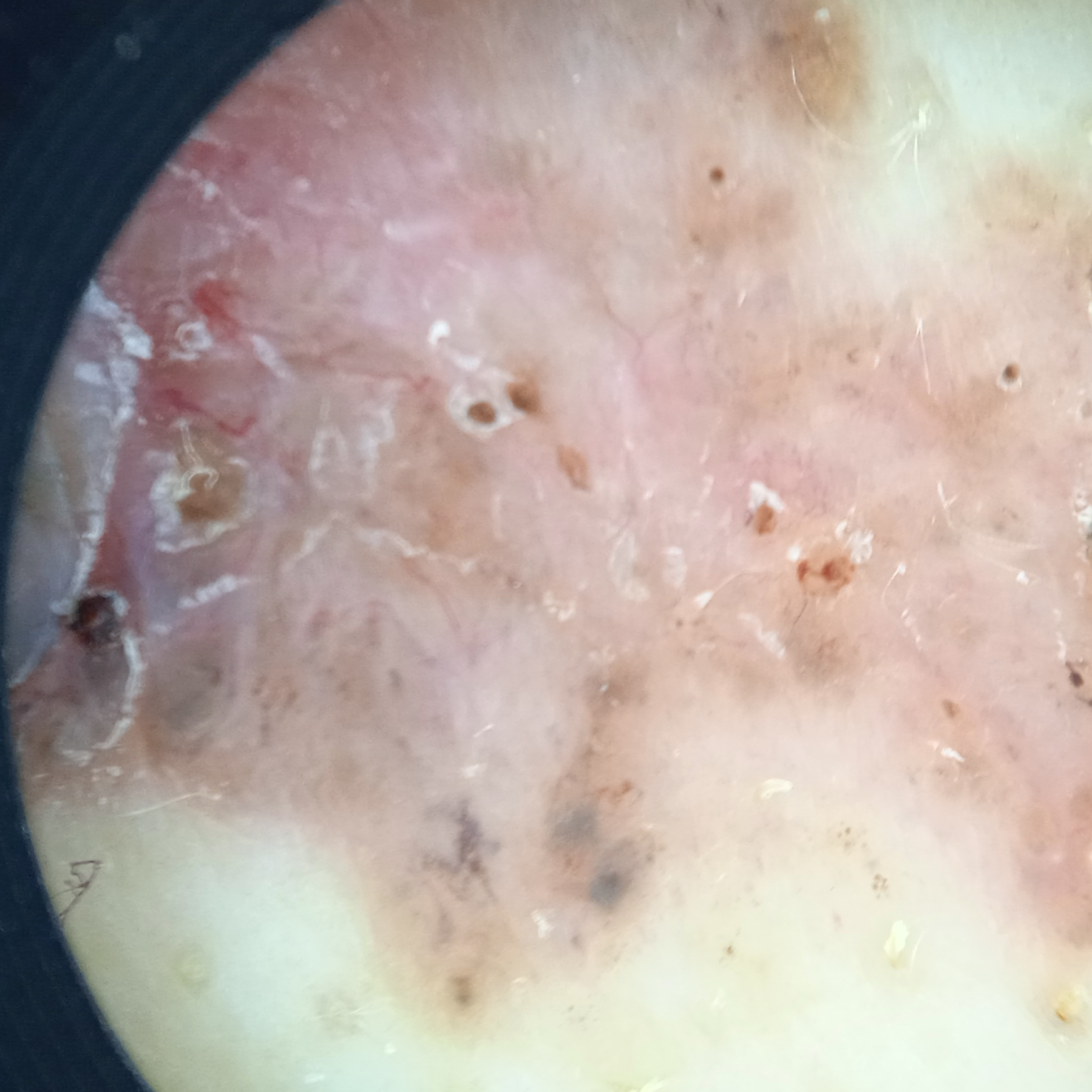Findings: Acquired for a research image collection, with no referral diagnosis. The patient says their skin tans without first burning. The patient reports a personal history of cancer. A moderate number of moles by the patient's own estimate. Located on the back. Measuring roughly 22.1 mm. Assessment: The diagnostic impression was a basal cell carcinoma.